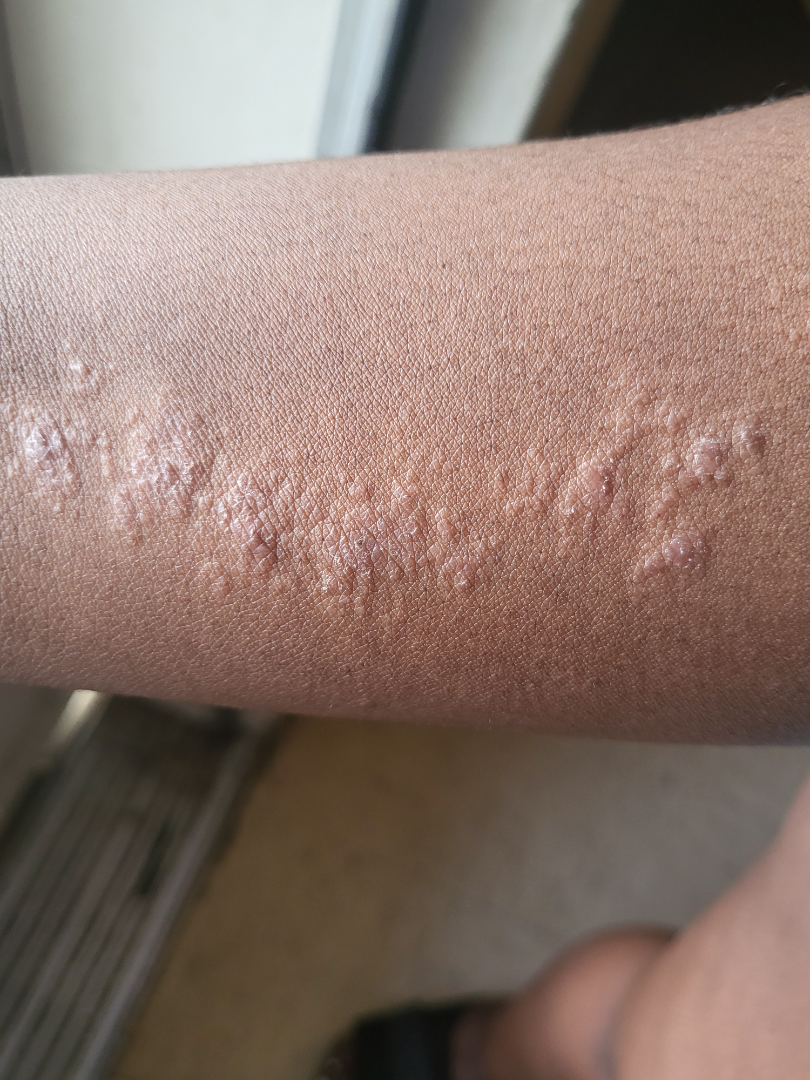<report>
<shot_type>at an angle</shot_type>
<body_site>arm</body_site>
<differential>Lichen striatus</differential>
</report>